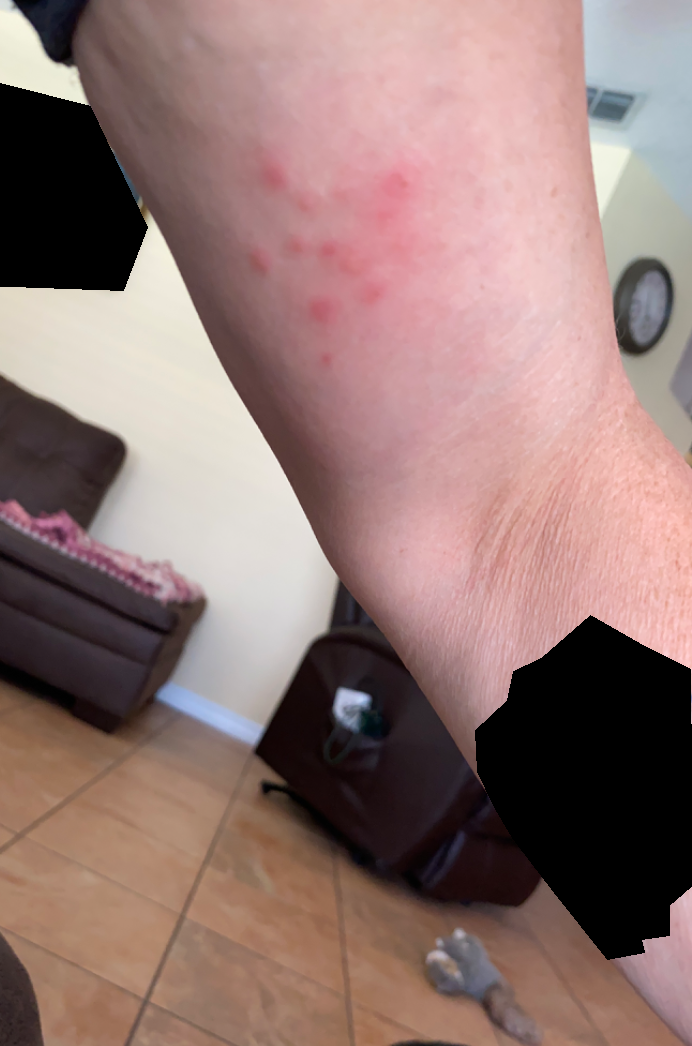{"body_site": "arm", "duration": "less than one week", "shot_type": "at a distance", "symptoms": ["itching", "burning", "pain"], "systemic_symptoms": "chills", "differential": {"Insect Bite": 0.55, "Herpes Simplex": 0.27, "Allergic Contact Dermatitis": 0.18}}